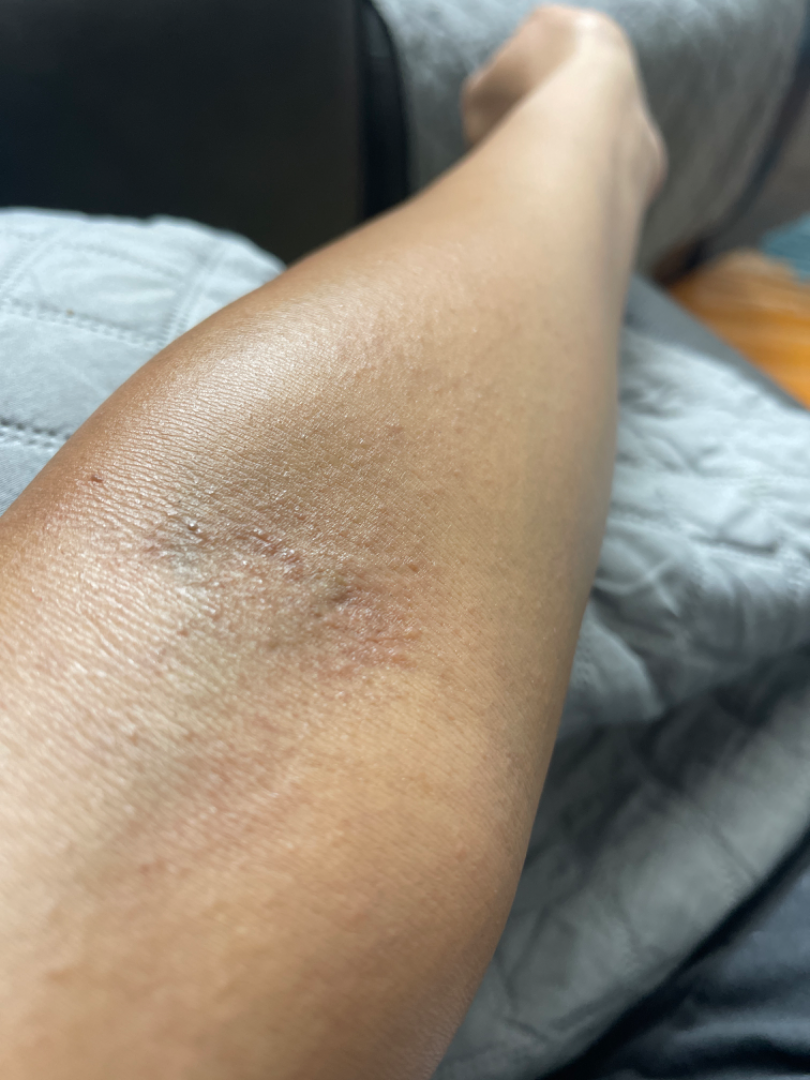| feature | finding |
|---|---|
| lesion texture | raised or bumpy |
| photo taken | at a distance |
| history | less than one week |
| body site | arm |
| impression | in keeping with Eczema |